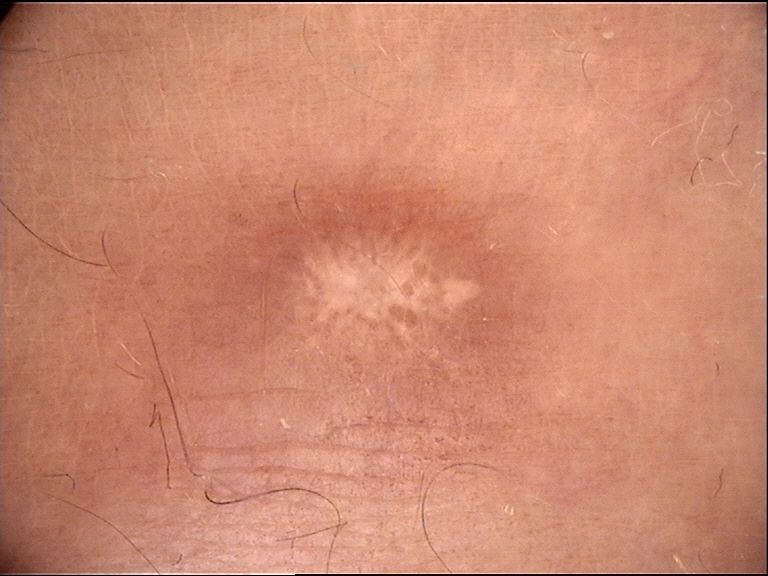imaging=dermatoscopy; diagnostic label=dermatofibroma (expert consensus).